Close-up view: 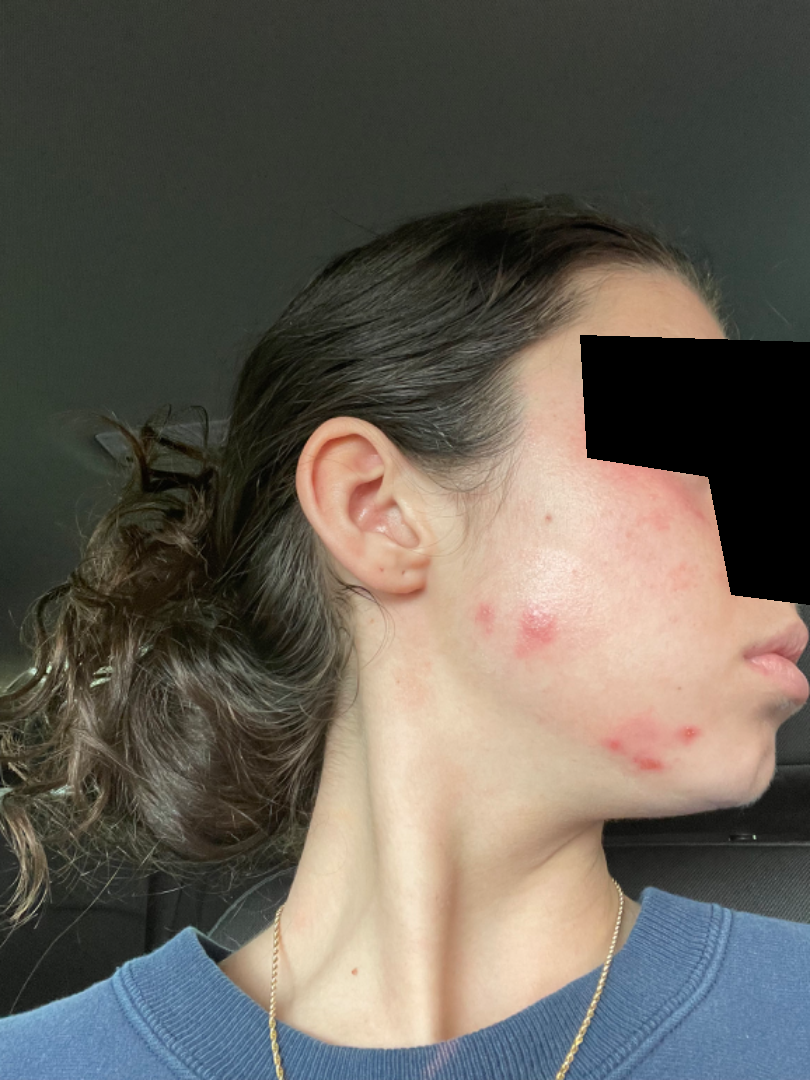Findings:
– assessment — the leading impression is Acne; possibly Impetigo